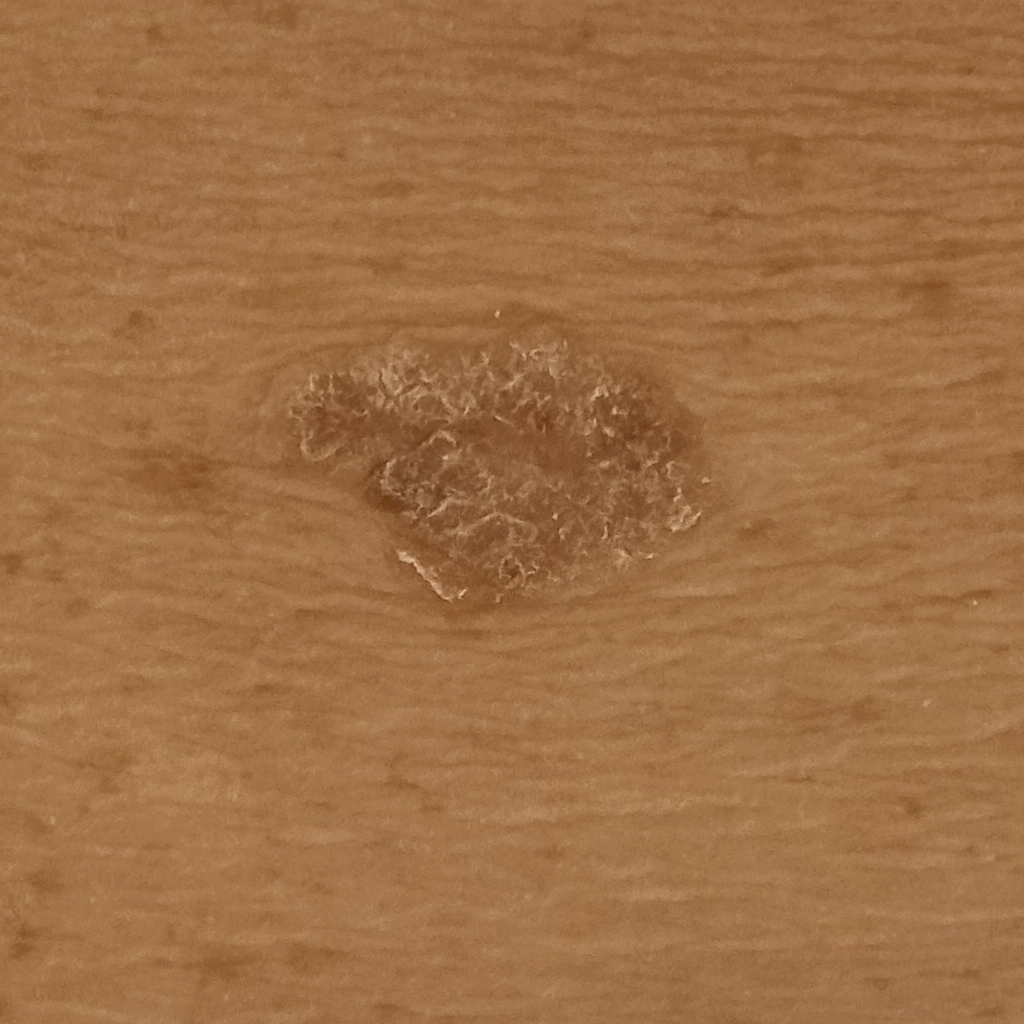A macroscopic clinical photograph of a skin lesion. By self-report, a personal history of cancer. A male patient 72 years old. The patient says their skin reddens with sun exposure. Imaged for a research study, with no referral diagnosis recorded. The lesion is located on the back. The lesion is about 16.5 mm across. The lesion was assessed as a seborrheic keratosis.